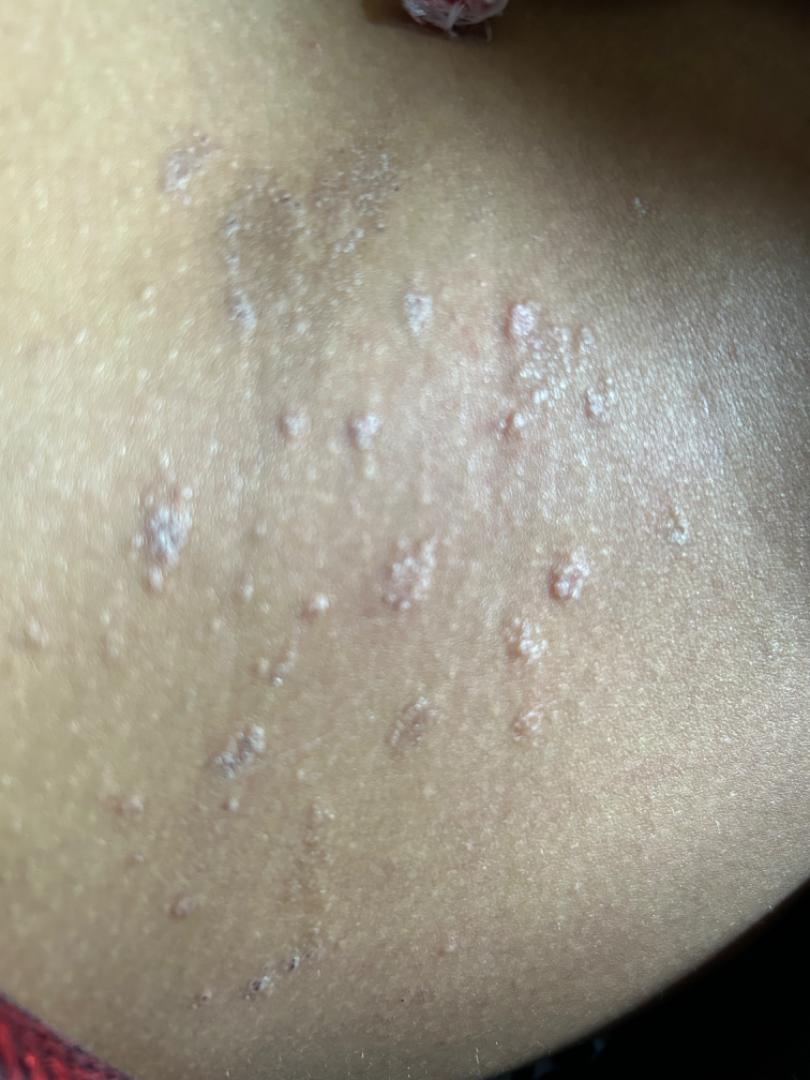Case summary:
• assessment — indeterminate from the photograph
• patient — female, age 18–29
• onset — one to four weeks
• image framing — close-up
• lesion texture — raised or bumpy and rough or flaky
• body site — arm, leg and back of the torso
• skin tone — self-reported Fitzpatrick skin type VI
• self-categorized as — a rash